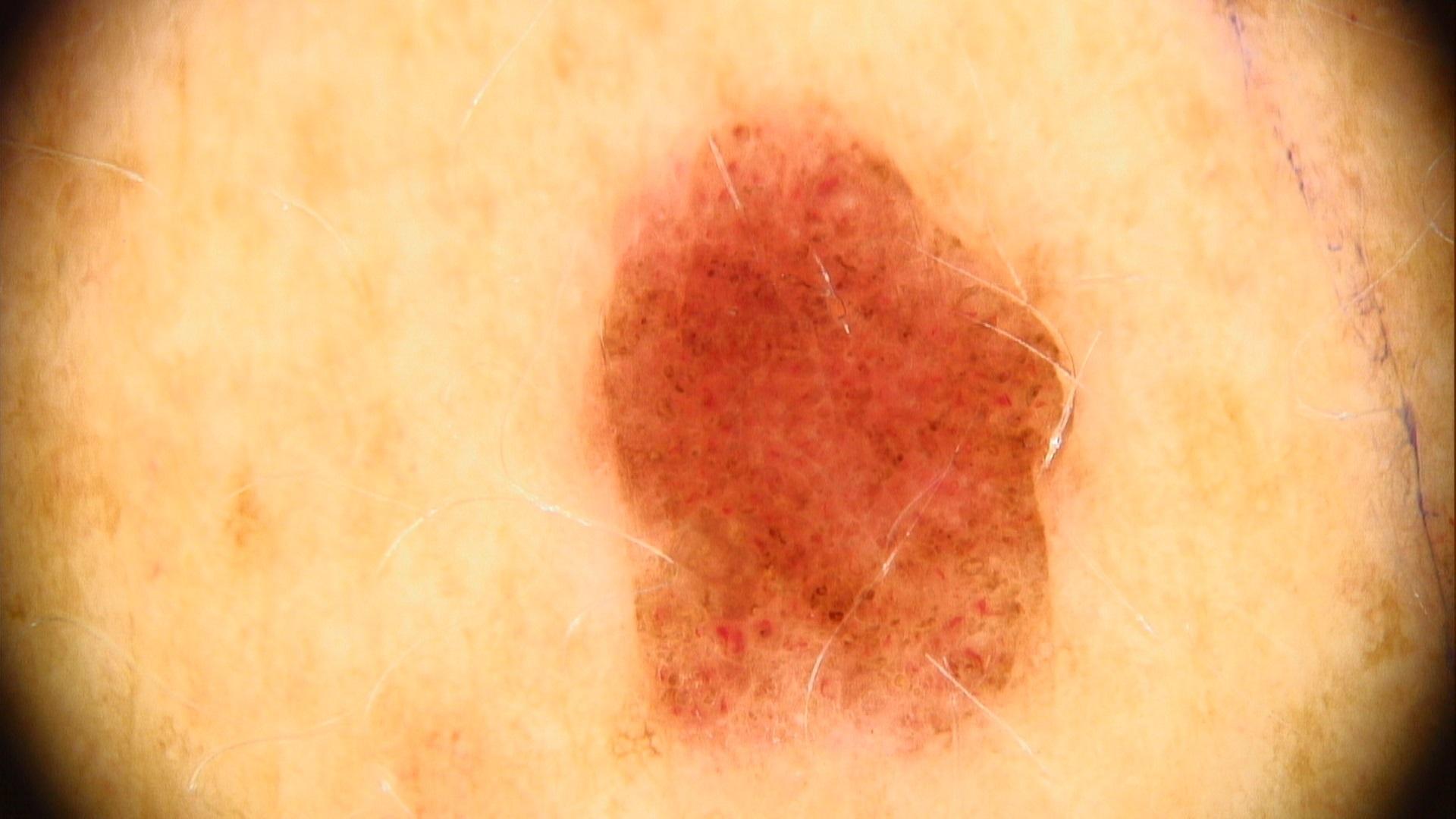Impression: The clinical assessment was a nevus.